The patient says their skin tans without first burning; the patient describes having few moles overall; a female patient 60 years of age; a macroscopic clinical photograph of a skin lesion; on a questionnaire the patient reported a personal history of cancer and a personal history of skin cancer; the referring clinician suspected basal cell carcinoma: 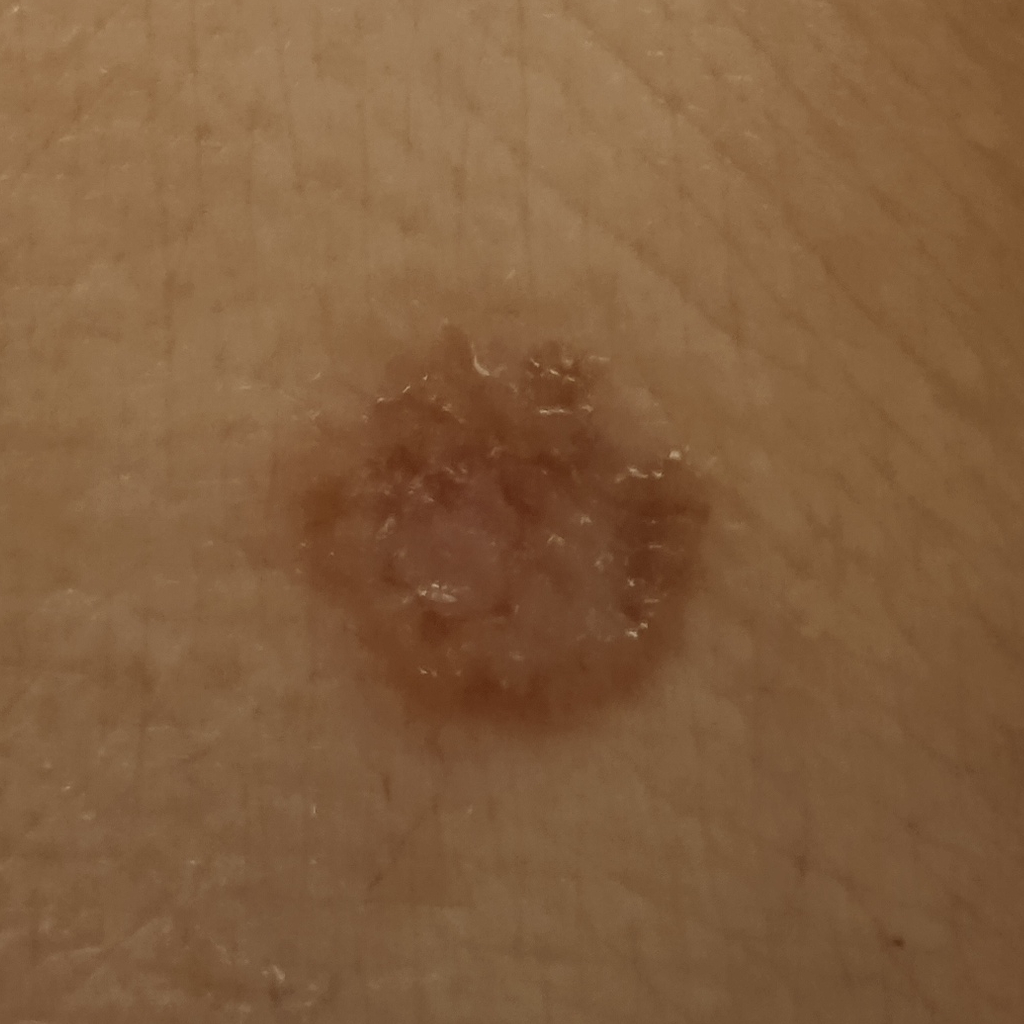The lesion is on the torso. The lesion measures approximately 13.2 mm. Dermatologist review favored a basal cell carcinoma.